A dermoscopy image of a single skin lesion: 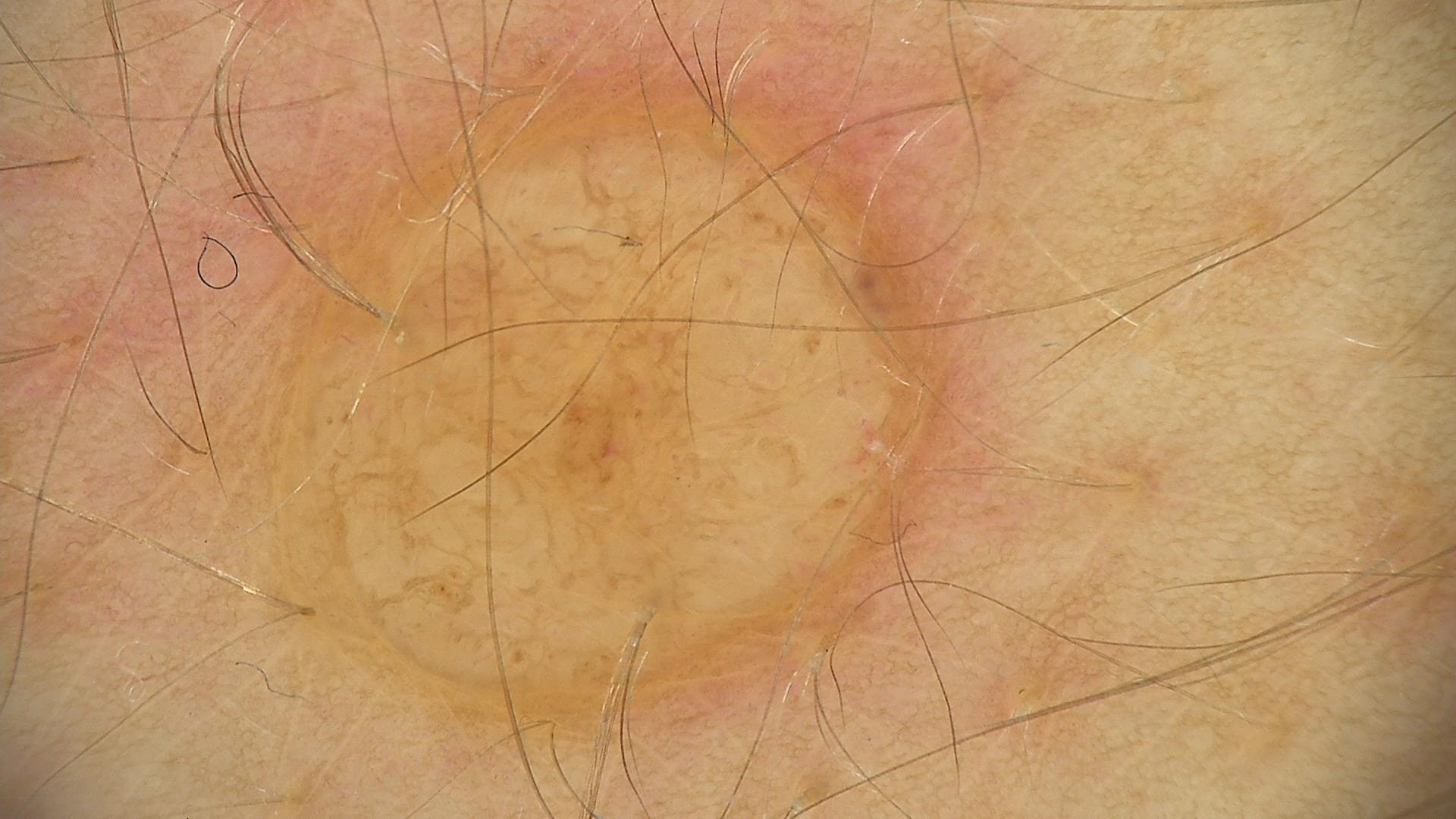label=dermal nevus (expert consensus).